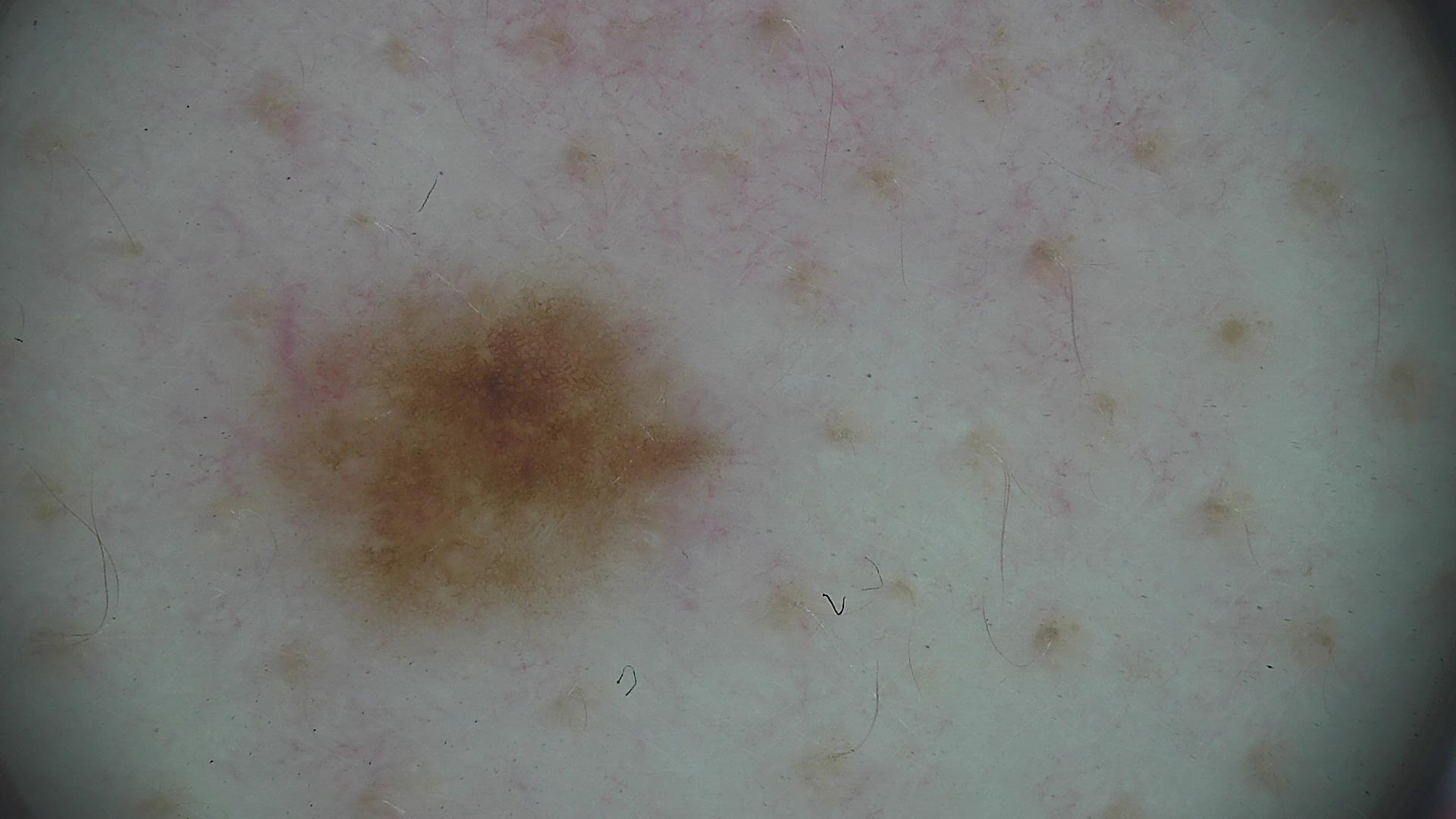Labeled as a dysplastic junctional nevus.